A clinical photograph of a skin lesion · a female subject in their mid-70s — 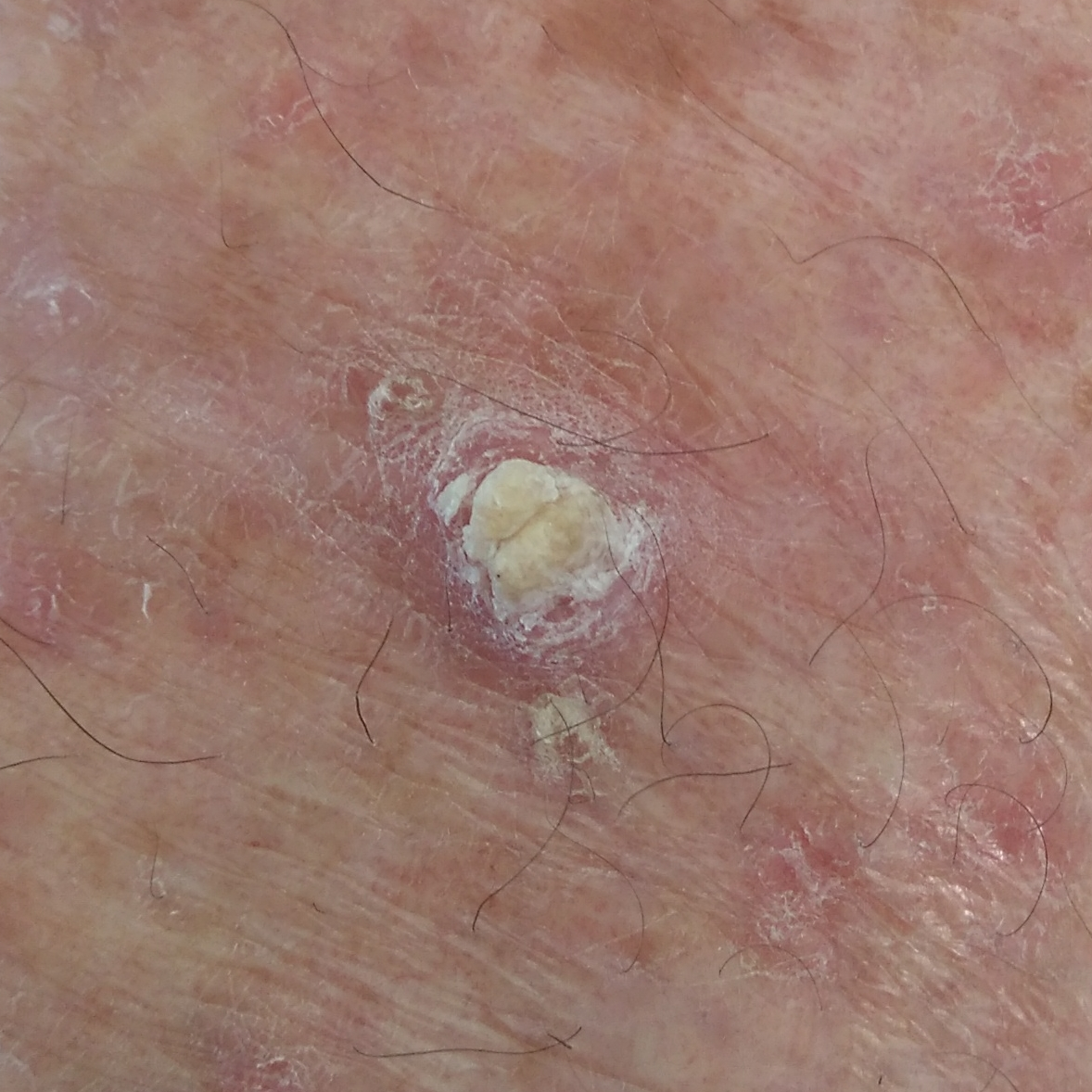anatomic site=a thigh | symptoms=elevation, itching / no bleeding | diagnostic label=actinic keratosis (biopsy-proven).